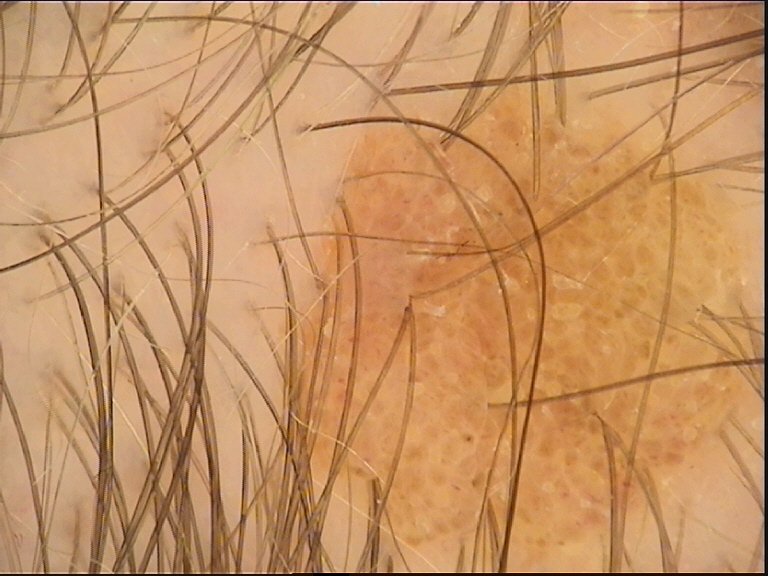imaging = dermatoscopy | assessment = compound nevus (expert consensus).